Acquired for a research image collection, with no referral diagnosis. A clinical close-up of a skin lesion. A female patient 59 years of age:
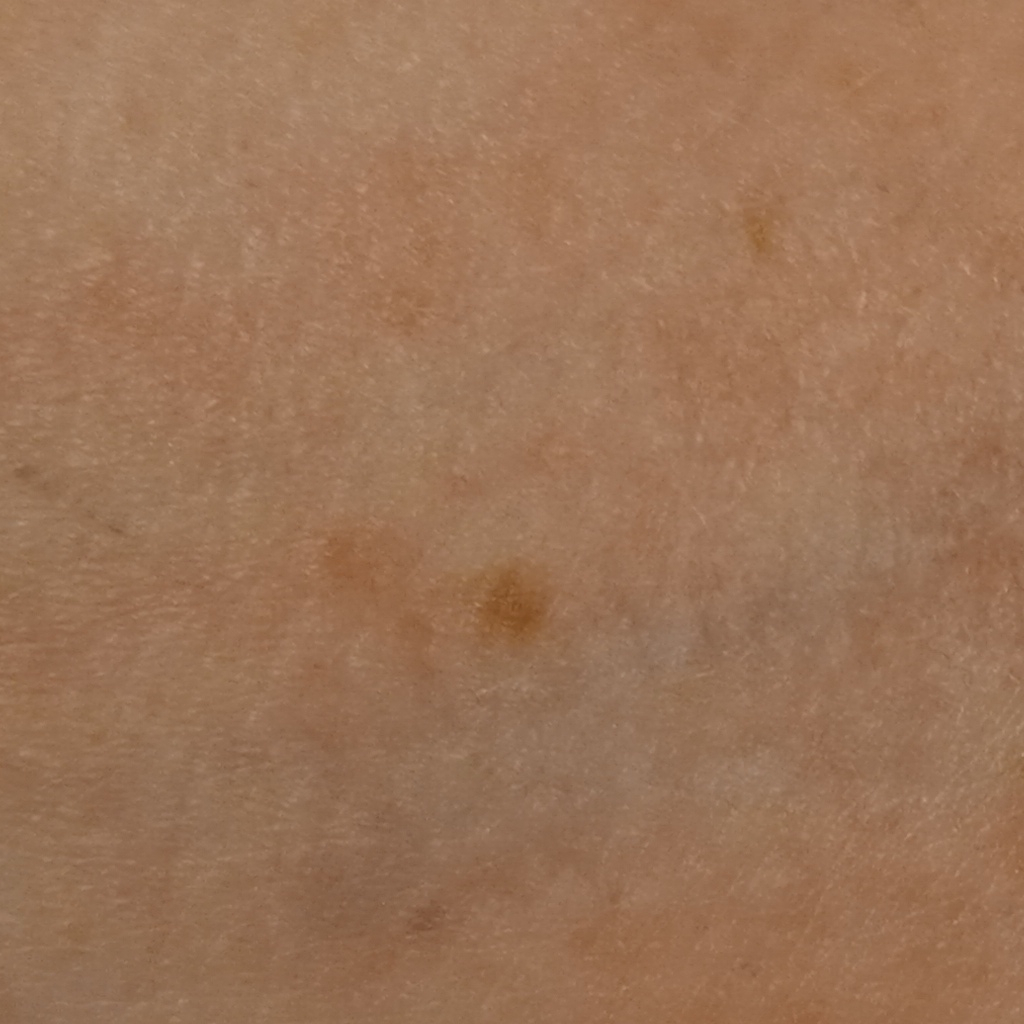The lesion is on an arm. The lesion is about 6.5 mm across. The consensus diagnosis for this lesion was a melanocytic nevus.